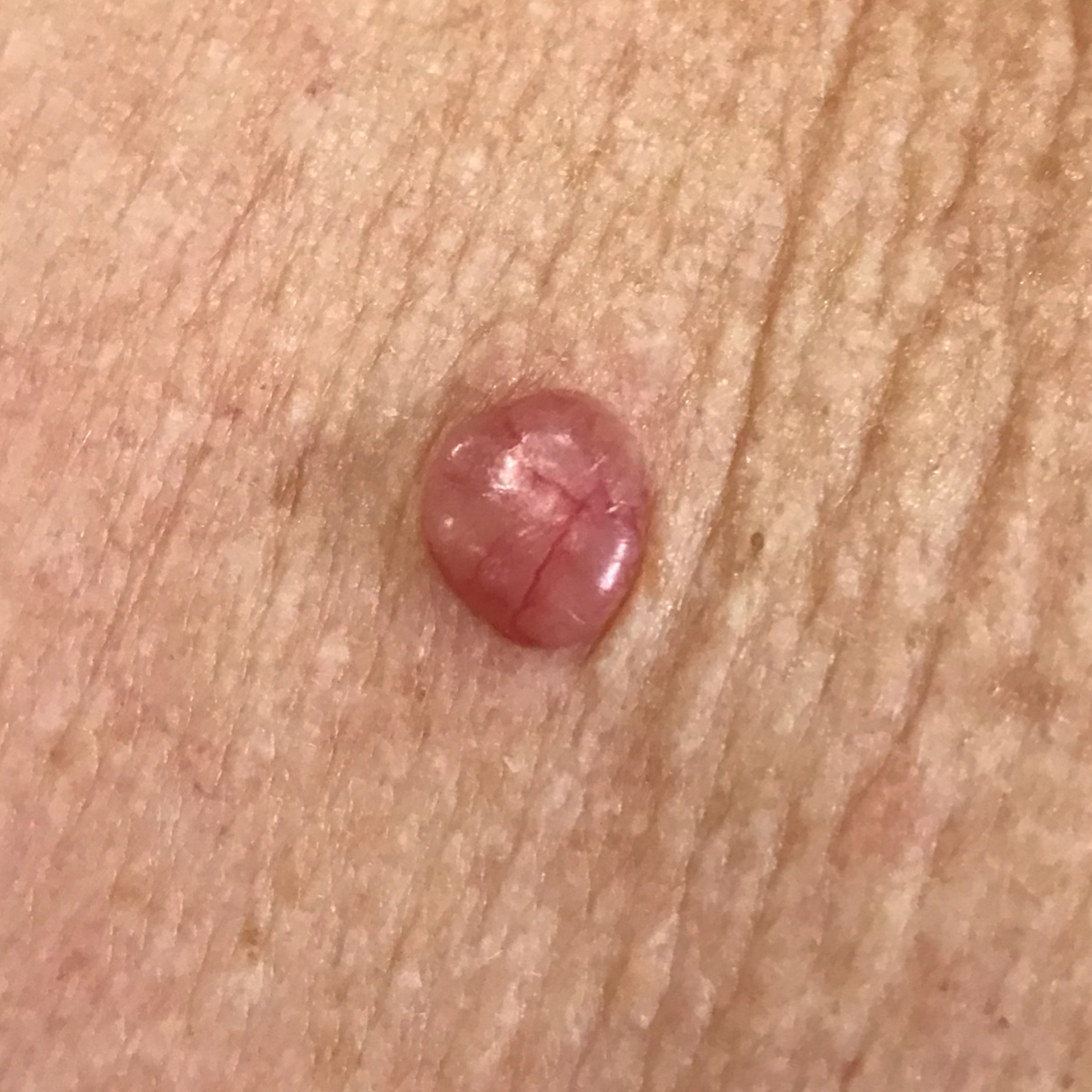pathology — basal cell carcinoma (biopsy-proven)